Female contributor, age 18–29. Located on the top or side of the foot and leg. This is a close-up image — 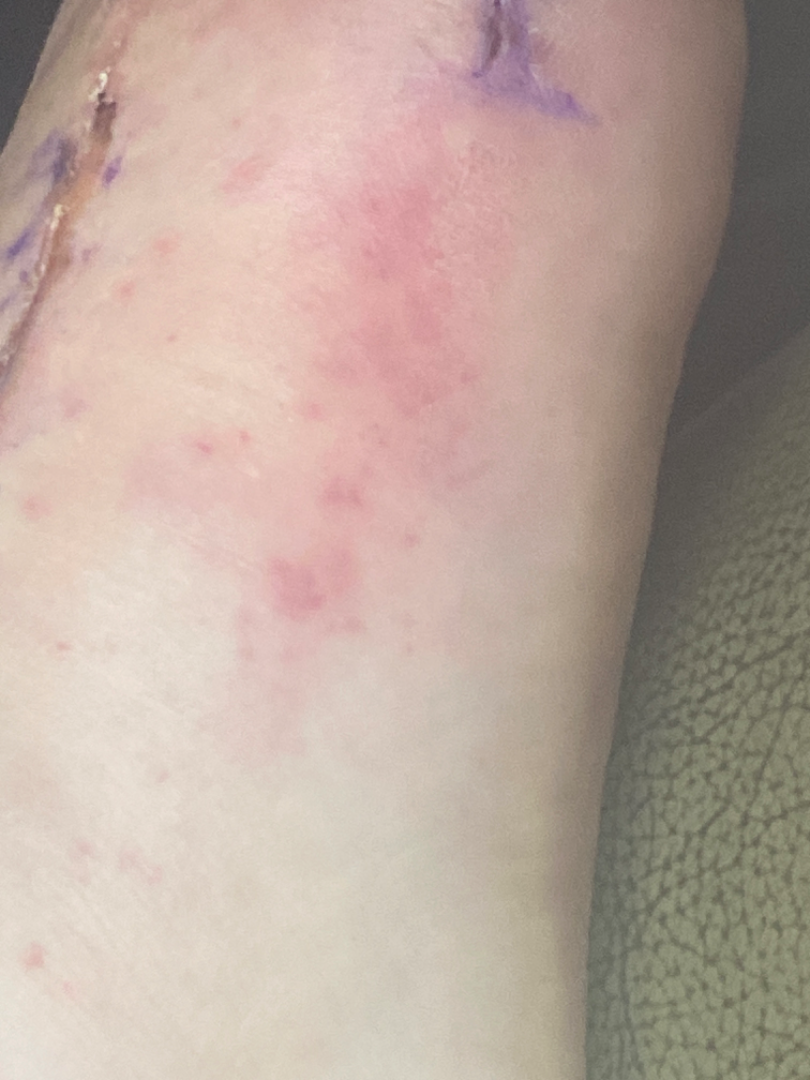The condition could not be reliably identified from the image.